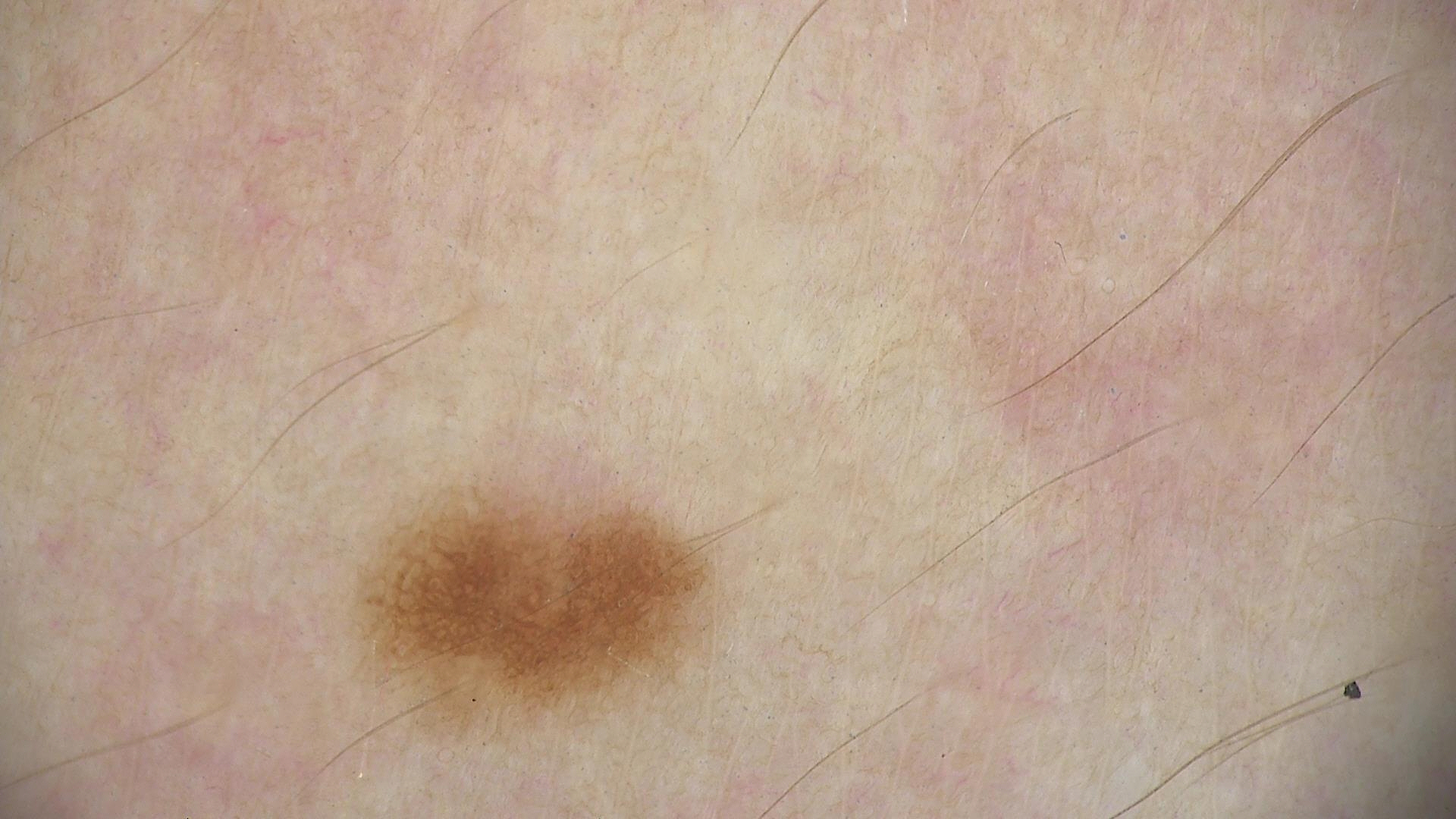classification = banal; label = junctional nevus (expert consensus).